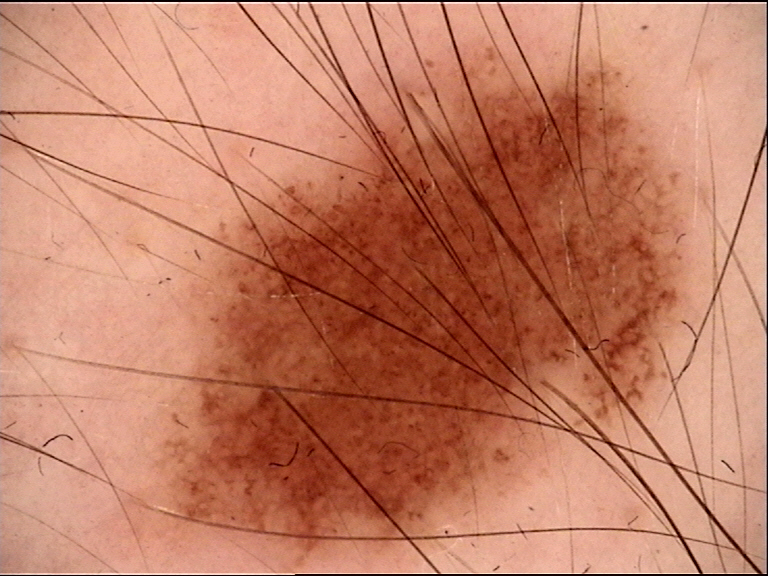A dermoscopic image of a skin lesion. Classified as a dysplastic junctional nevus.